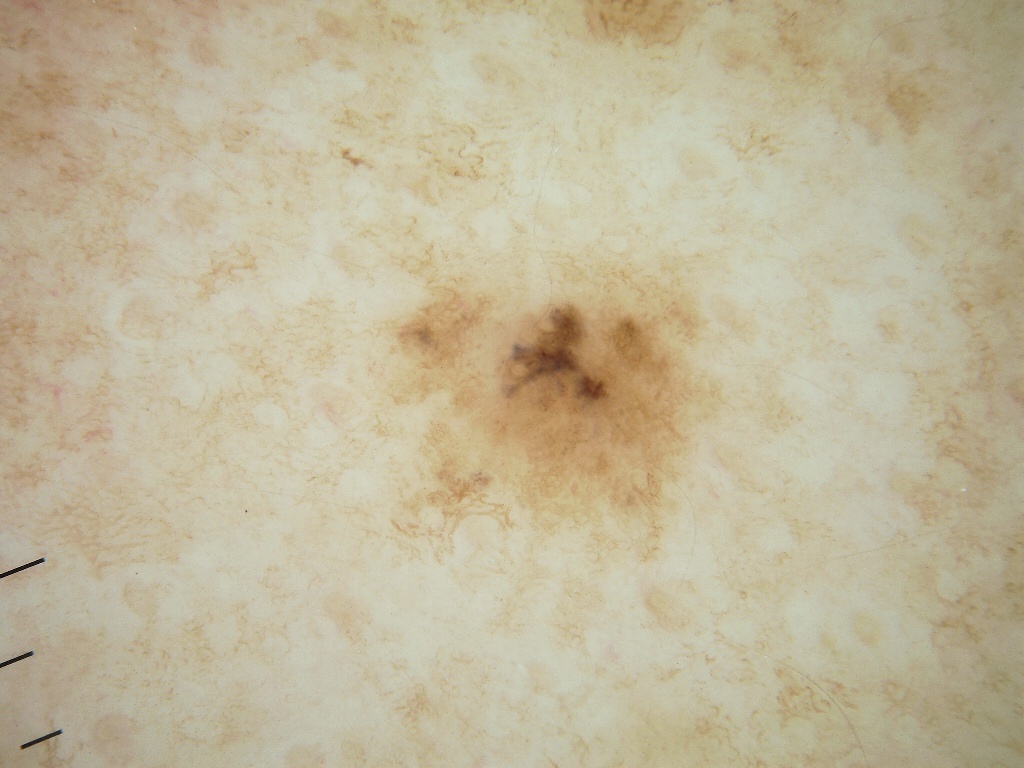A female subject about 65 years old. A dermoscopic view of a skin lesion. With coordinates (x1, y1, x2, y2), the lesion is bounded by [388, 259, 725, 559]. Dermoscopic assessment notes pigment network. The lesion covers approximately 8% of the dermoscopic field. The clinical diagnosis was a melanocytic nevus.